A dermoscopic photograph of a skin lesion:
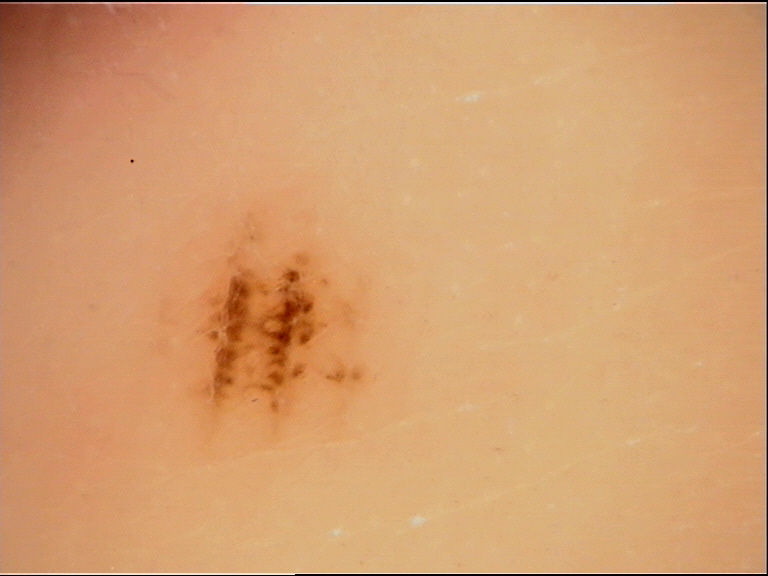The morphology is that of a banal lesion.
Consistent with an acral junctional nevus.